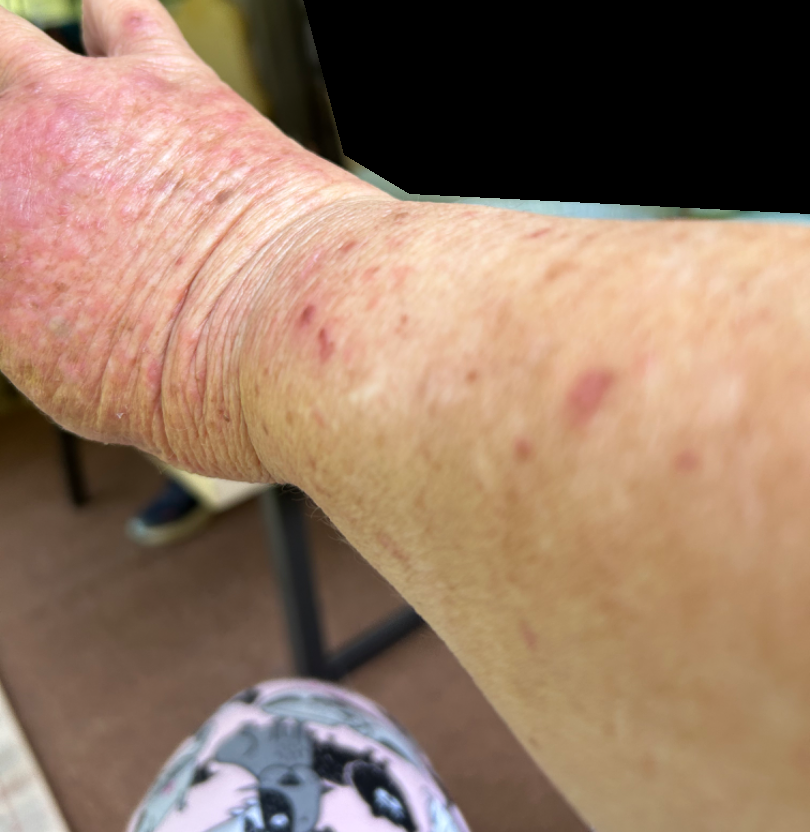{
  "shot_type": "close-up",
  "differential": {
    "leading": [
      "Allergic Contact Dermatitis"
    ],
    "considered": [
      "Photodermatitis"
    ]
  }
}